A dermoscopic close-up of a skin lesion.
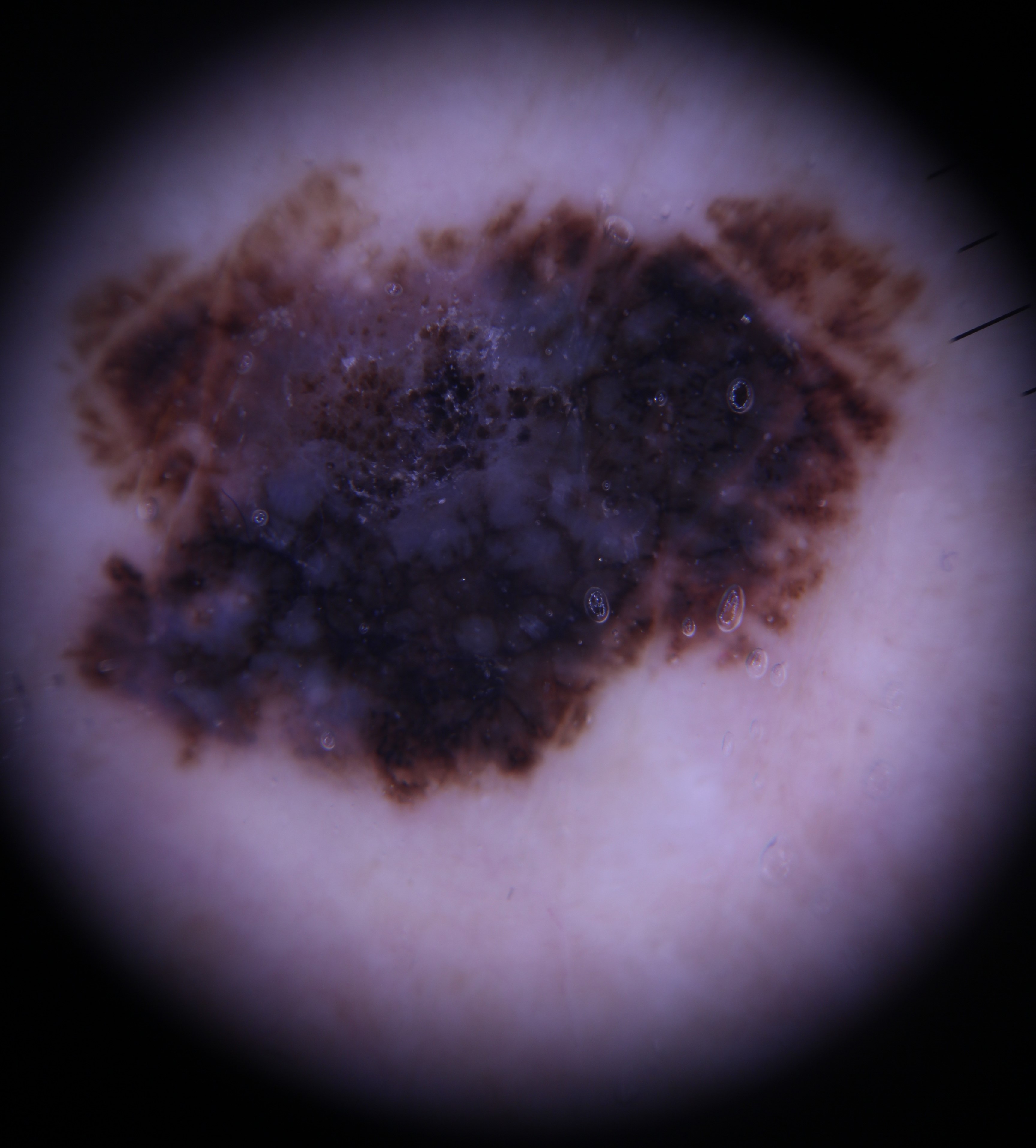Biopsy-confirmed as a malignant lesion — a melanoma.